A skin lesion imaged with a dermatoscope; a male patient, aged 53-57.
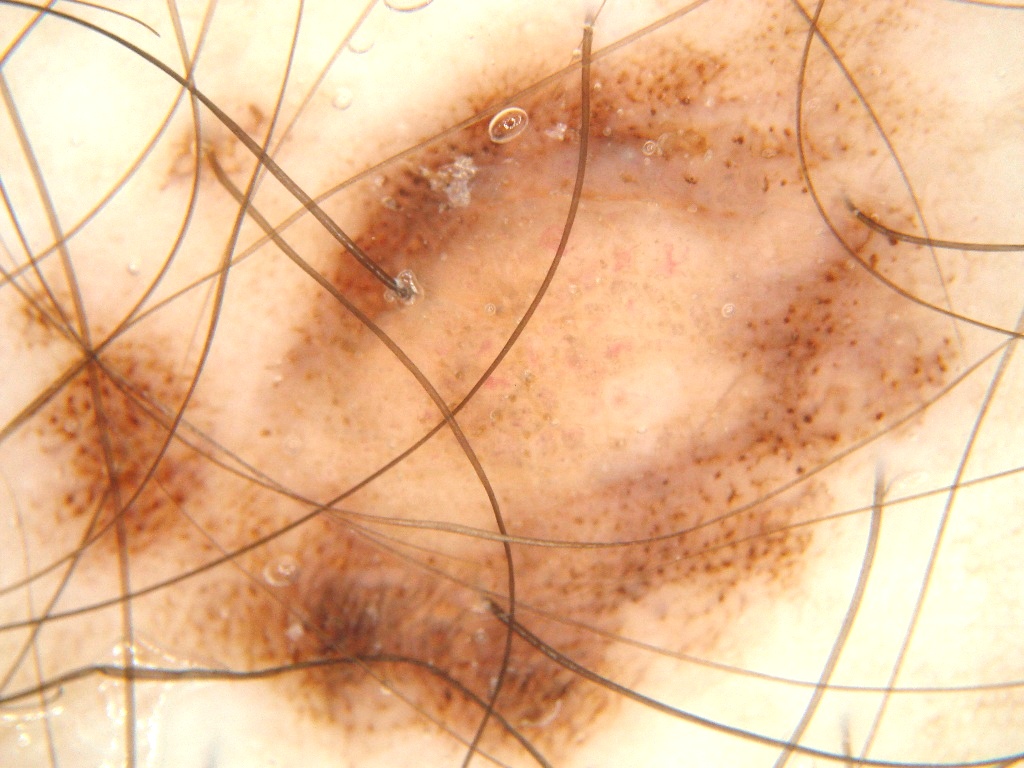Dermoscopically, the lesion shows pigment network, with no streaks, milia-like cysts, or negative network.
The lesion spans essentially the entire dermoscopic field.
Clinically diagnosed as a melanocytic nevus, a benign skin lesion.